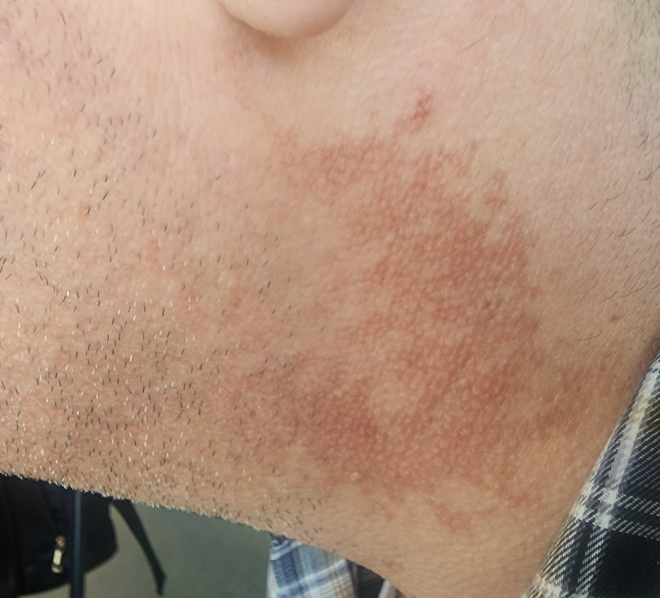diagnostic considerations = favoring Poikiloderma; the differential also includes Post-Inflammatory hyperpigmentation